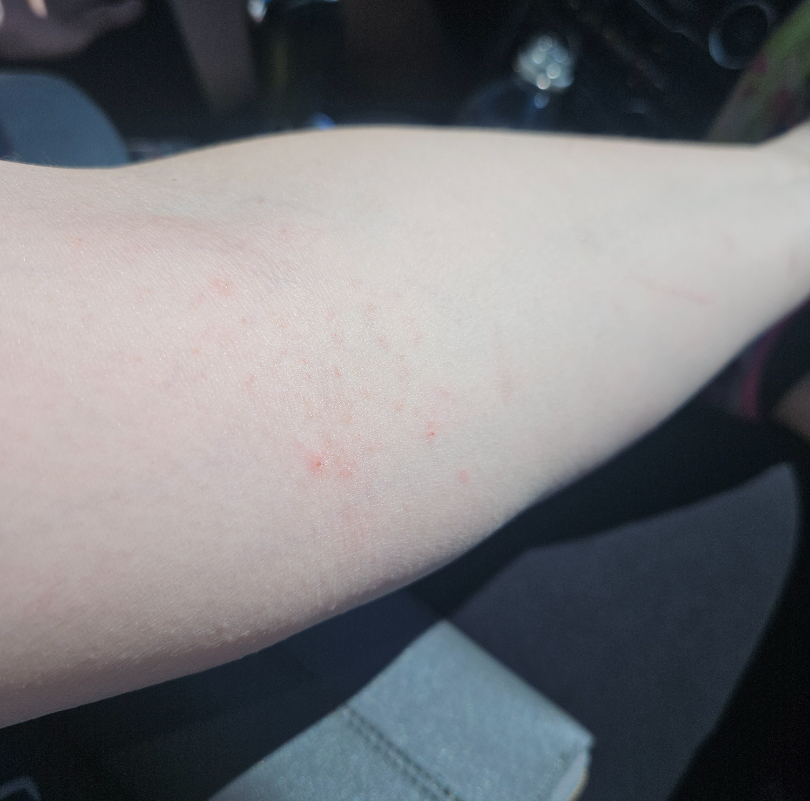Findings: The reviewer was unable to grade this case for skin condition. Background: Skin tone: Fitzpatrick skin type I. The photograph is a close-up of the affected area.